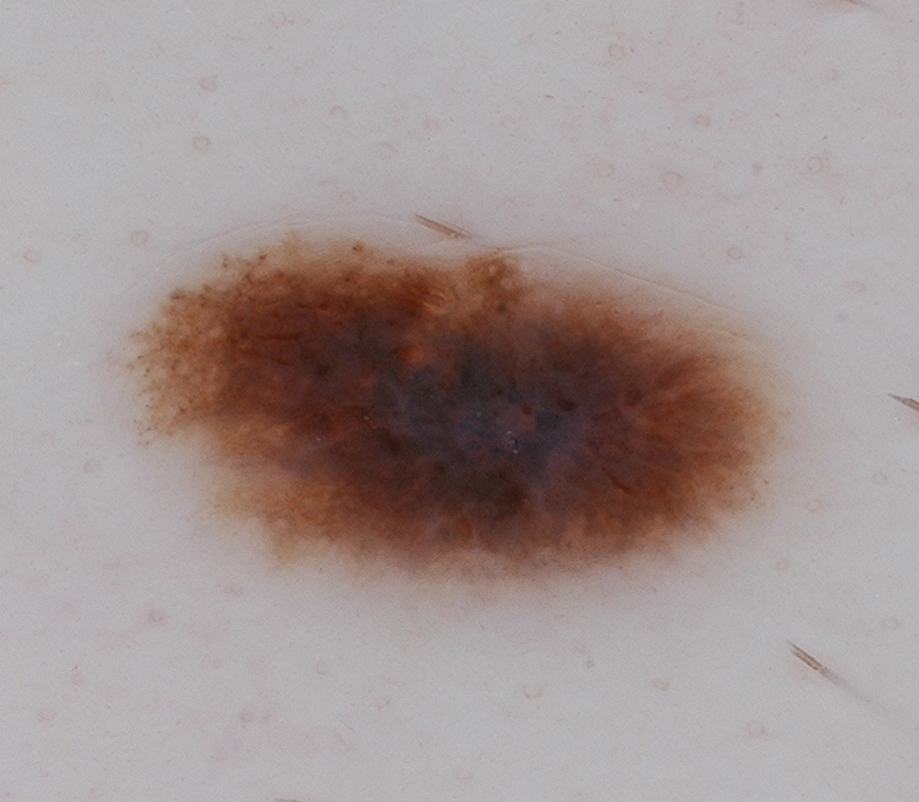Image and clinical context: A dermoscopy image of a single skin lesion. The visible lesion spans left=130, top=228, right=775, bottom=592. Conclusion: Confirmed on histopathology as a melanoma.